Dermoscopy of a skin lesion: 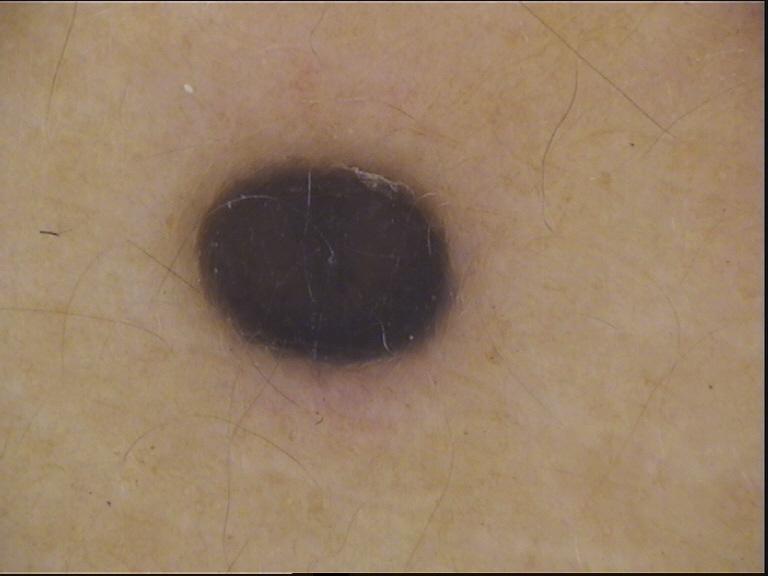Impression:
Consistent with a blue nevus.